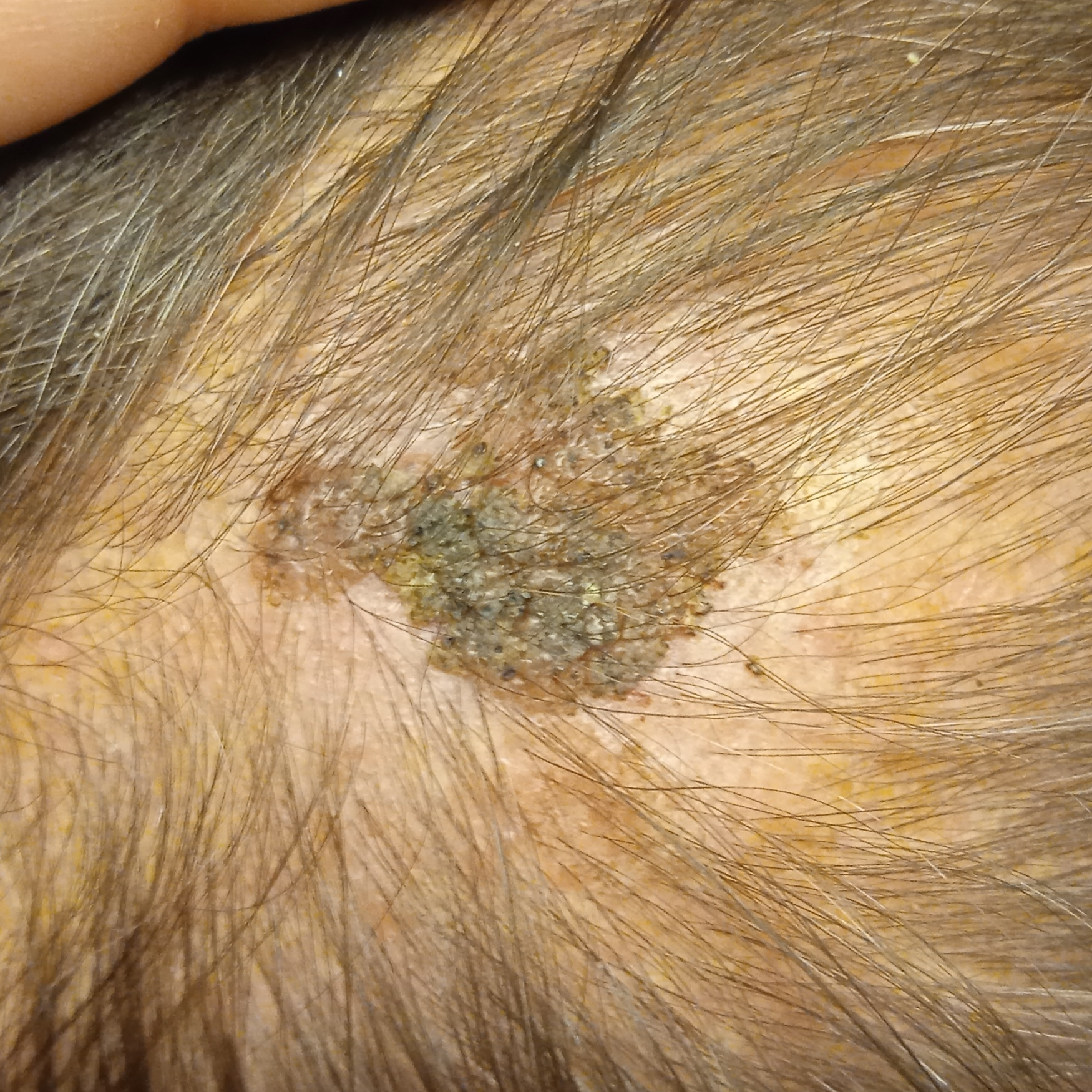relevant history: no personal history of cancer, no immunosuppression; imaging: clinical photograph; patient: male, aged 72; clinical context: research study (no referral diagnosis); sun reaction: skin tans without first burning; body site: the head; lesion size: 19.2 mm; diagnosis: seborrheic keratosis (dermatologist consensus).